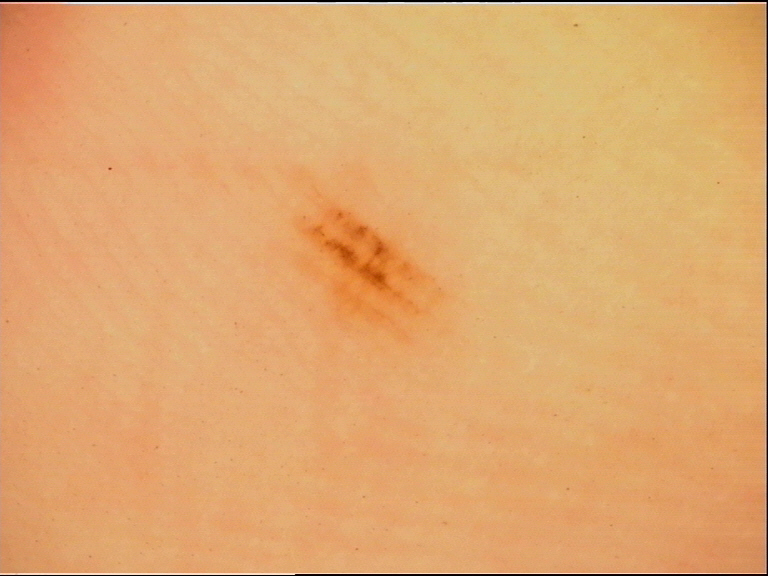modality = dermoscopy; class = acral junctional nevus (expert consensus).